Self-categorized by the patient as a rash · the lesion is associated with itching, enlargement, burning, pain, bleeding and bothersome appearance · Fitzpatrick III; lay reviewers estimated Monk skin tone scale 2 · the photo was captured at an angle · the affected area is the palm, arm and back of the hand · the contributor reports the lesion is raised or bumpy, rough or flaky and fluid-filled: 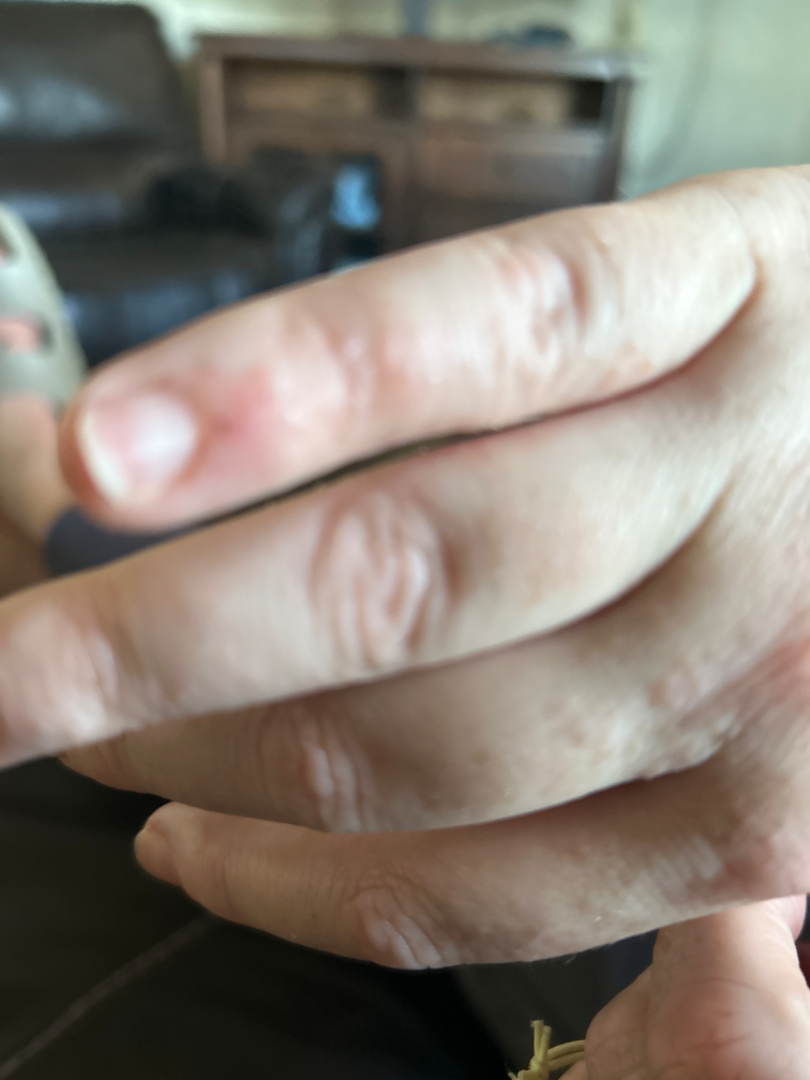The reviewing clinician's impression was: the favored diagnosis is Allergic Contact Dermatitis; also consider Impetigo; with consideration of Eczema.